A clinical photo of a skin lesion taken with a smartphone. A male patient 47 years of age: 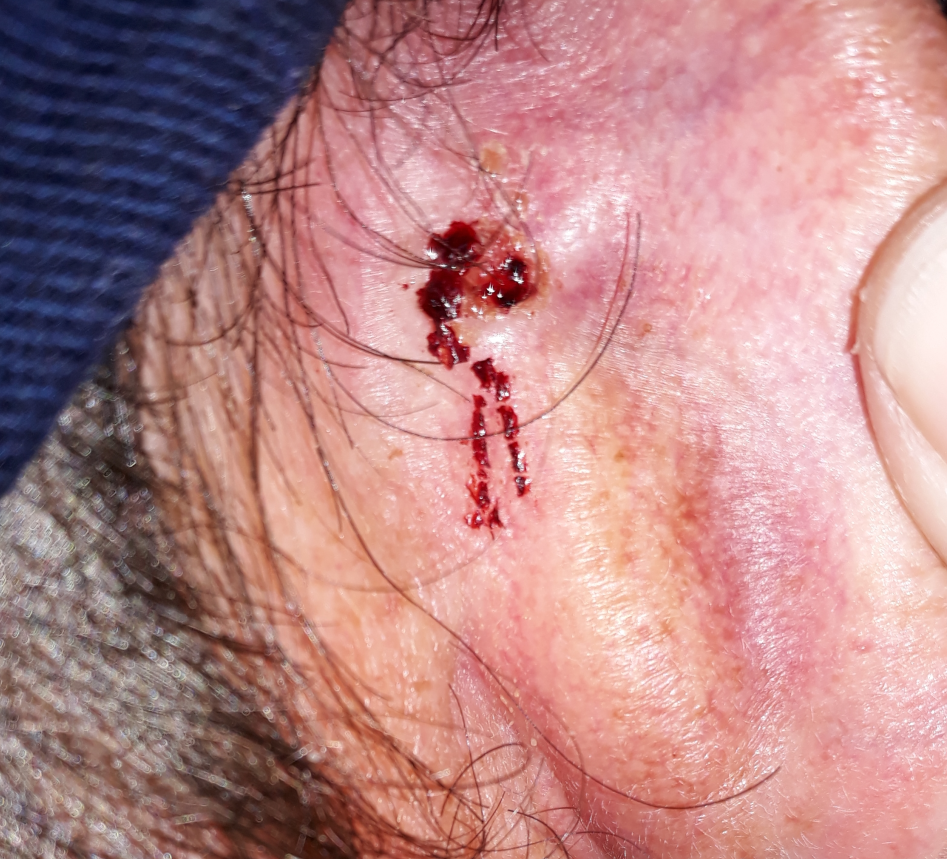Located on an ear.
The patient reports that the lesion has bled, itches, hurts, and is elevated.
Confirmed on histopathology as a basal cell carcinoma.